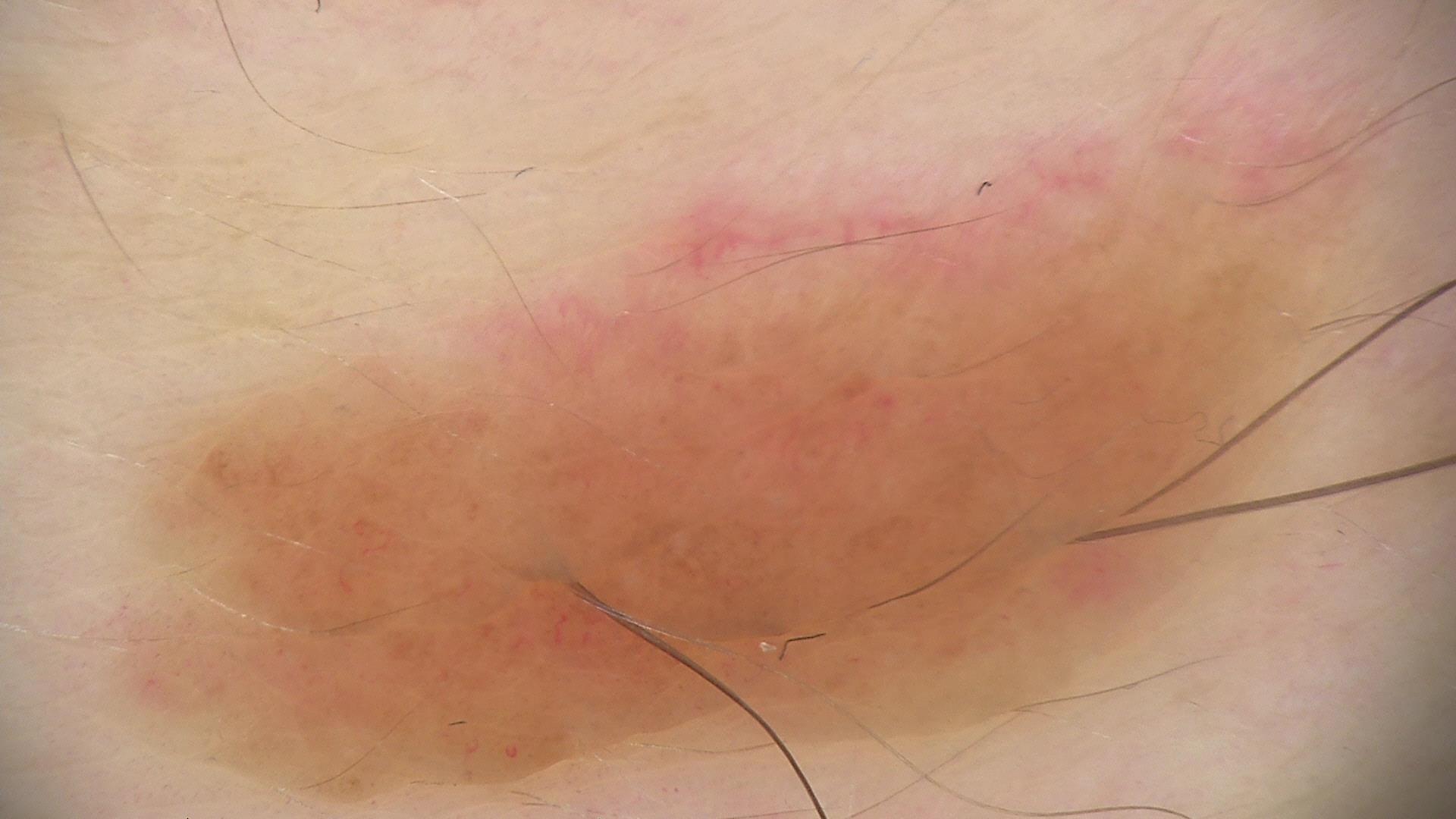Findings:
* modality — dermoscopy
* lesion type — banal
* class — dermal nevus (expert consensus)